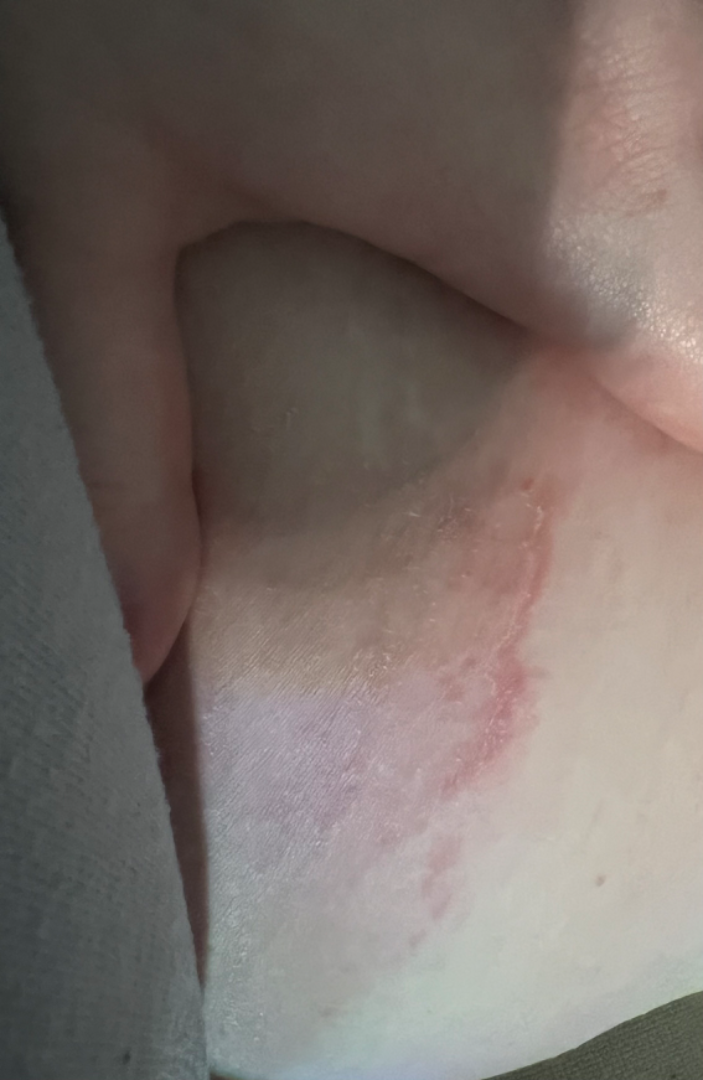assessment: ungradable on photographic review.